A dermoscopic photograph of a skin lesion:
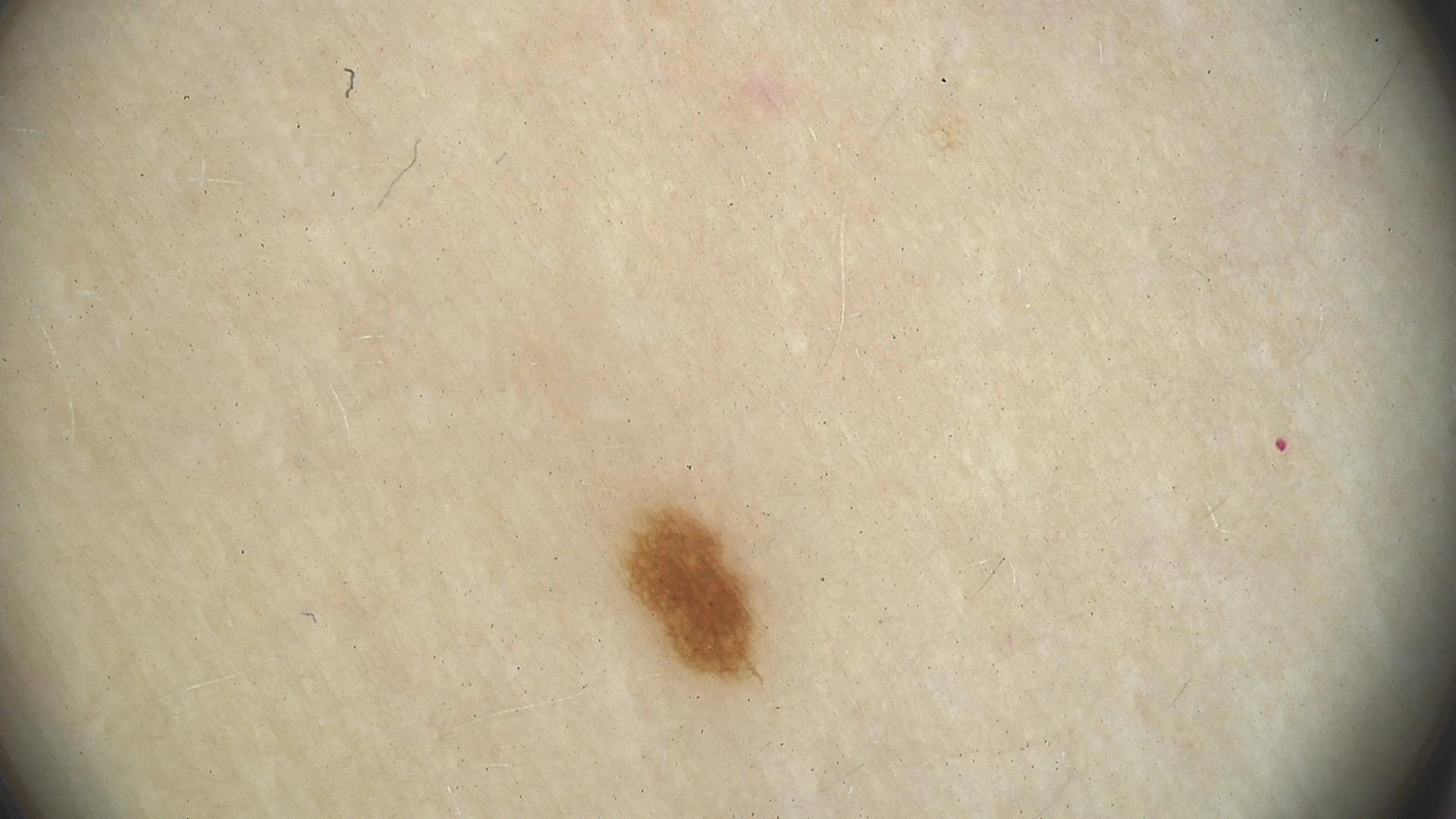Findings:
• diagnostic label · junctional nevus (expert consensus)